The photograph is a close-up of the affected area. The patient also reports joint pain. The top or side of the foot is involved. Female patient, age 60–69. The patient reports the lesion is raised or bumpy. The patient considered this a rash. The condition has been present for one to four weeks.
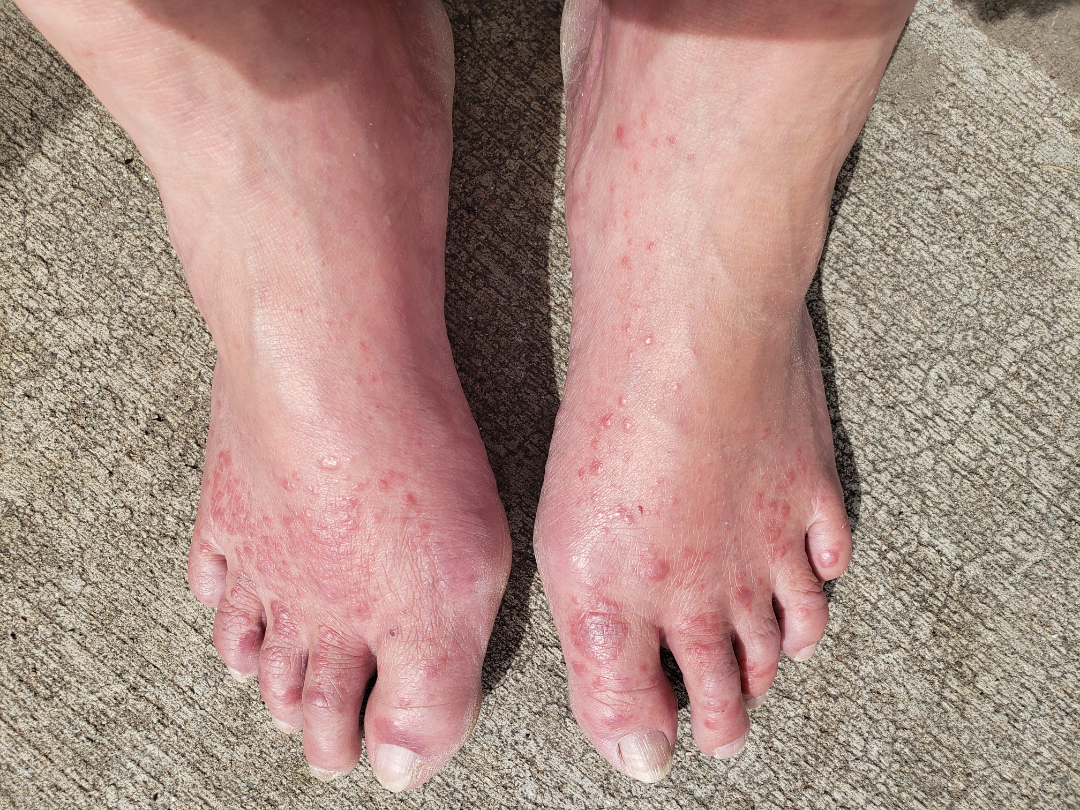Notes:
• dermatologist impression · favoring Lichen planus/lichenoid eruption; a remote consideration is Granuloma annulare; less likely is Eczema; lower on the differential is Allergic Contact Dermatitis